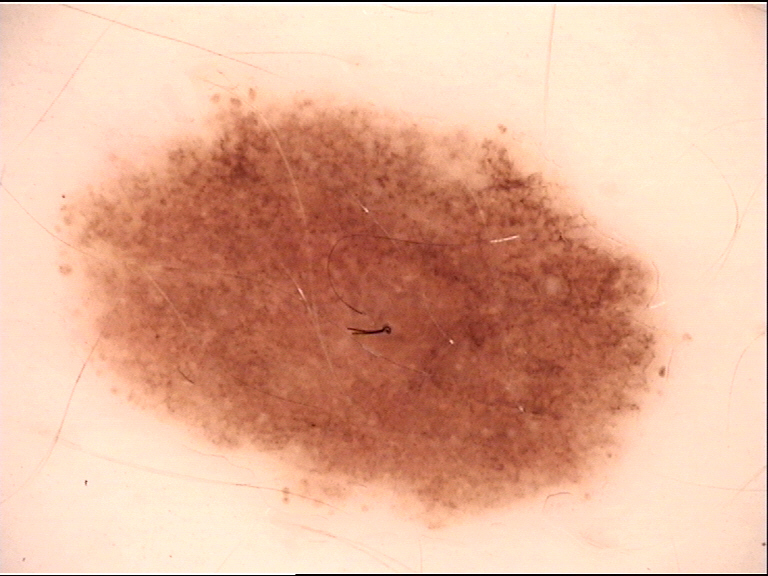Q: What is the diagnosis?
A: dysplastic junctional nevus (expert consensus)